The patient described the issue as a rash, the lesion involves the leg, a close-up photograph, the lesion is described as rough or flaky and raised or bumpy, Fitzpatrick skin type II; non-clinician graders estimated MST 2: 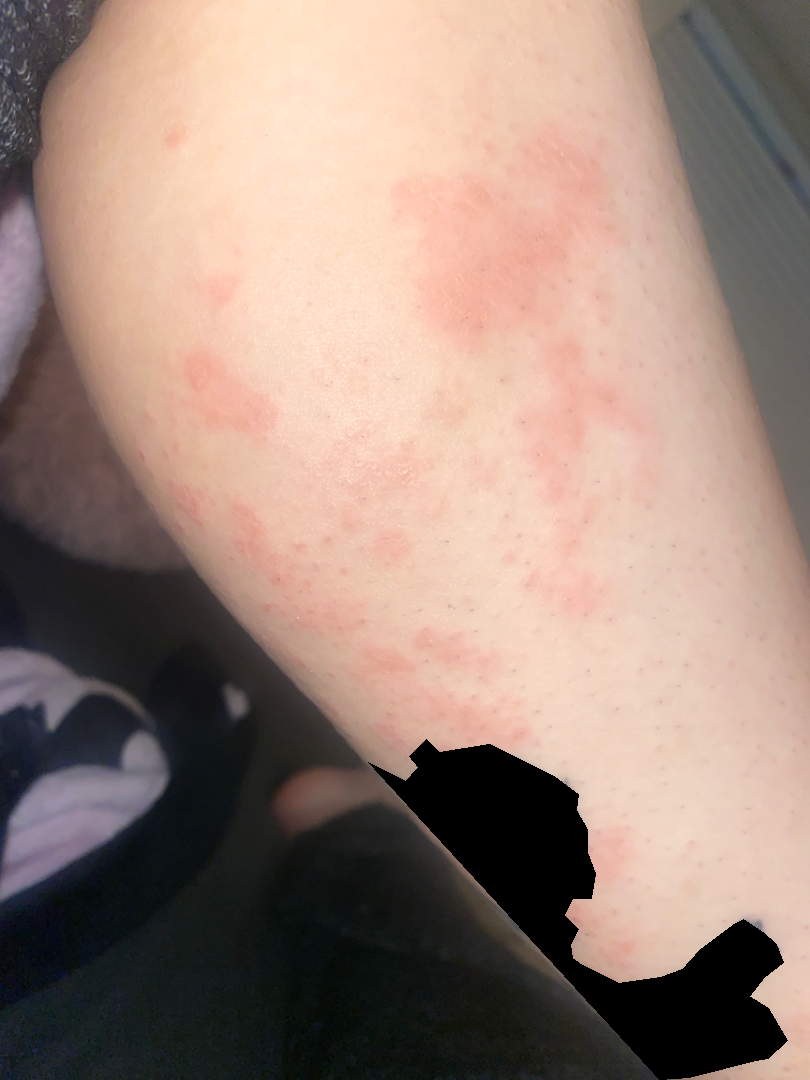Three dermatologists each reviewed the case: the leading consideration is Eczema; an alternative is Allergic Contact Dermatitis.